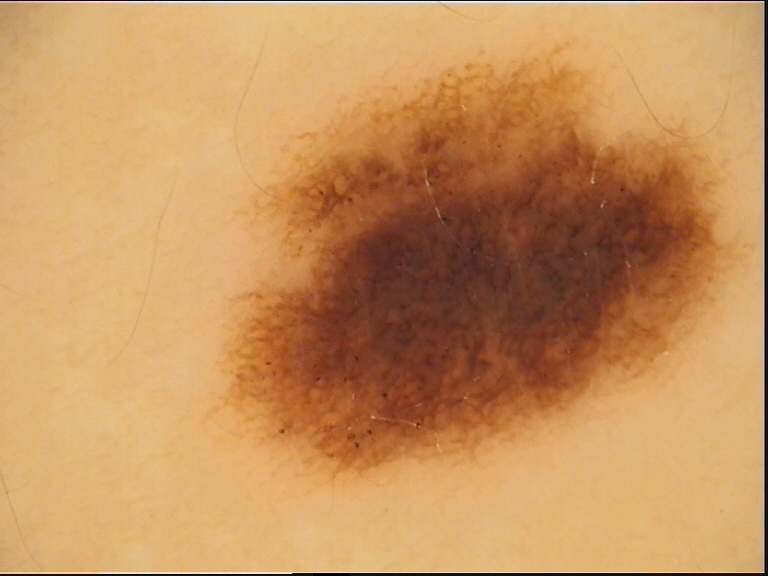image = dermatoscopy | class = dysplastic junctional nevus (expert consensus).